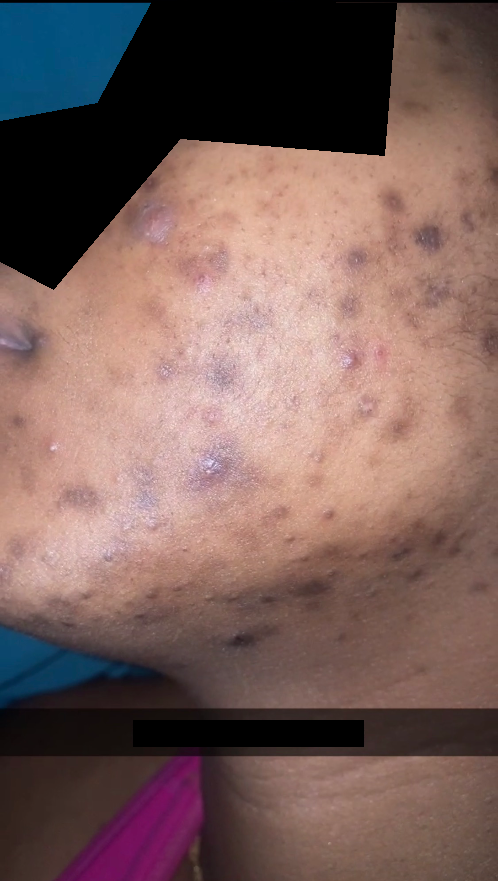Q: What is the affected area?
A: head or neck
Q: Fitzpatrick or Monk tone?
A: Fitzpatrick skin type V
Q: Who is the patient?
A: female, age 18–29
Q: How long has this been present?
A: more than five years
Q: What symptoms does the patient report?
A: darkening
Q: Image view?
A: close-up
Q: Patient's own categorization?
A: acne
Q: Any systemic symptoms?
A: none reported
Q: Texture?
A: rough or flaky and raised or bumpy
Q: What is the differential diagnosis?
A: Acne (most likely)